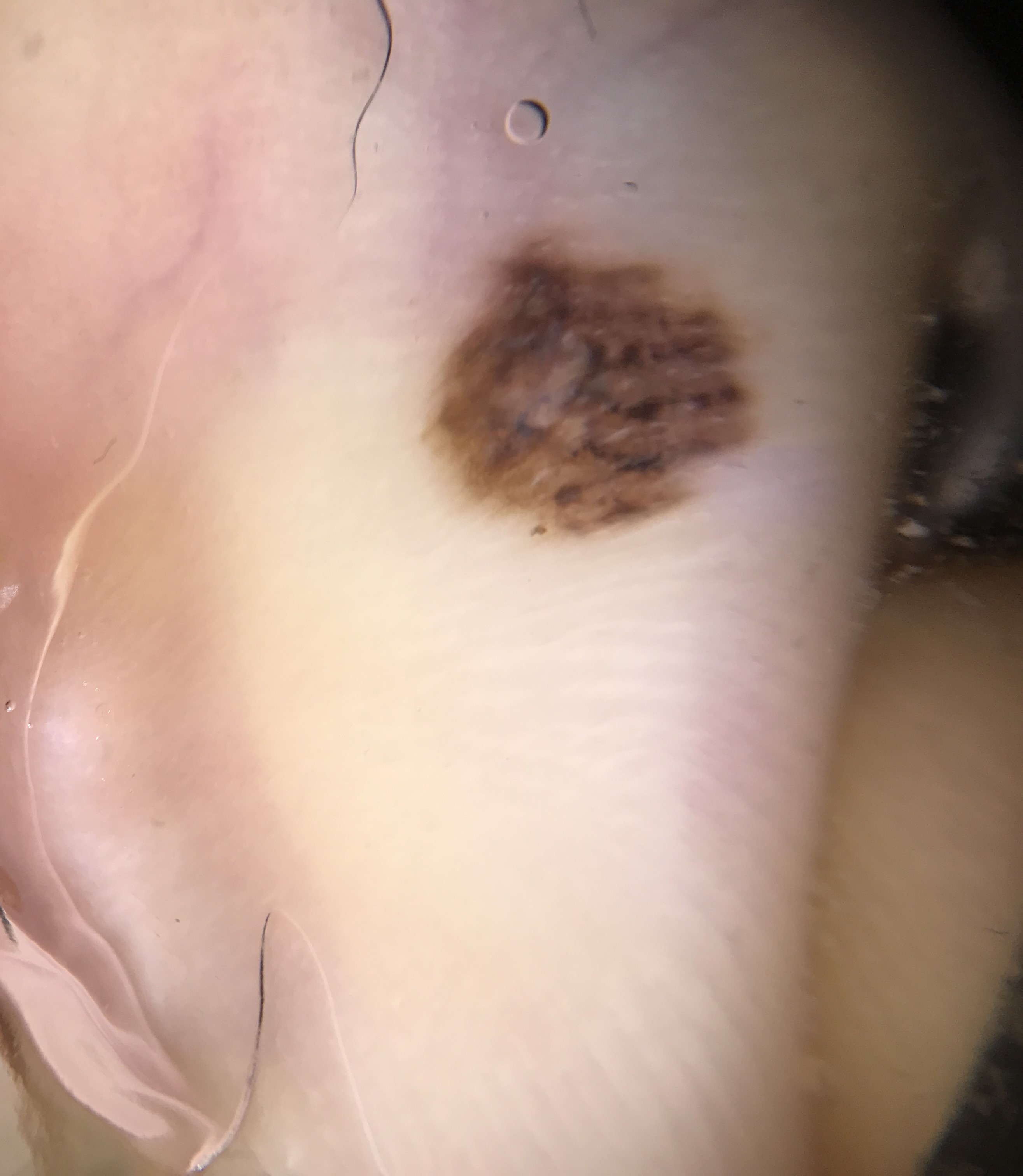Labeled as an acral dysplastic compound nevus.